Skin tone: FST II; human graders estimated Monk Skin Tone 2 · no relevant systemic symptoms · reported lesion symptoms include itching, burning and bothersome appearance · reported duration is one to four weeks · the photo was captured at an angle · the lesion is described as fluid-filled and raised or bumpy.
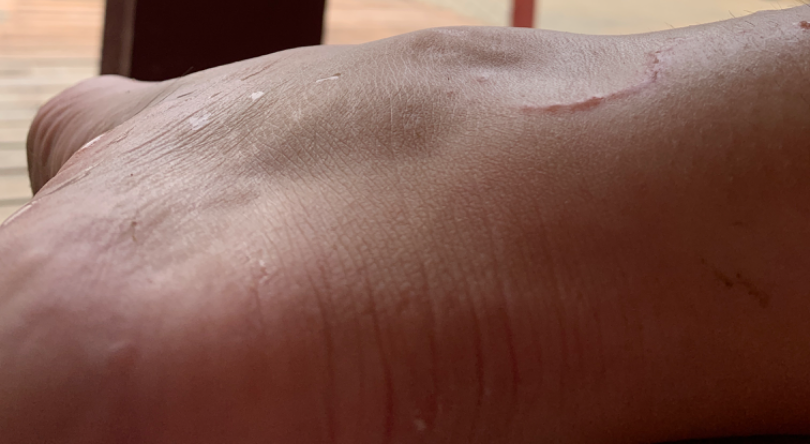{"differential": {"leading": ["Cutaneous larva migrans"]}}